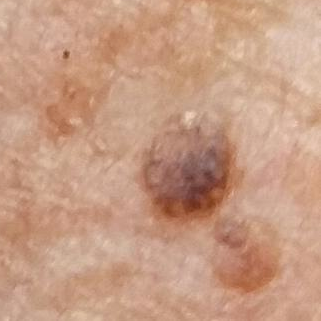A patient in their late 60s.
A clinical photograph showing a skin lesion.
The patient describes that the lesion is elevated.
The consensus clinical diagnosis was a seborrheic keratosis.